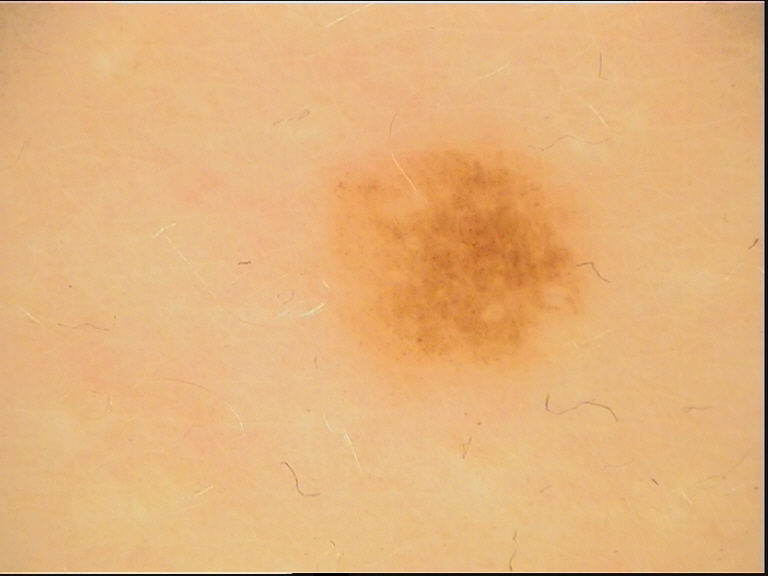diagnosis: dysplastic junctional nevus (expert consensus).